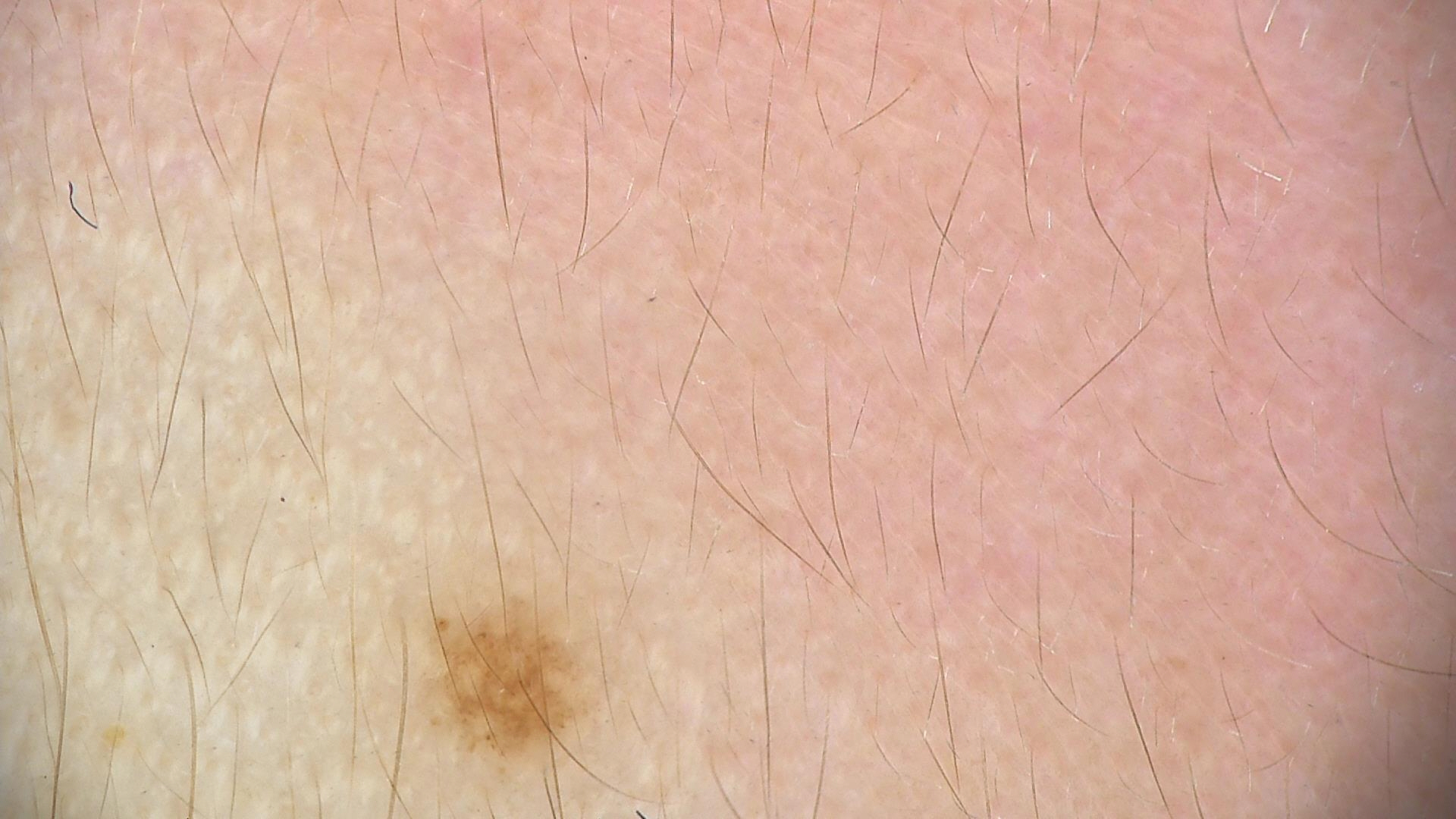A dermatoscopic image of a skin lesion. Diagnosed as a compound lesion — a Miescher nevus.